A female subject, aged around 40 · dermoscopy of a skin lesion: 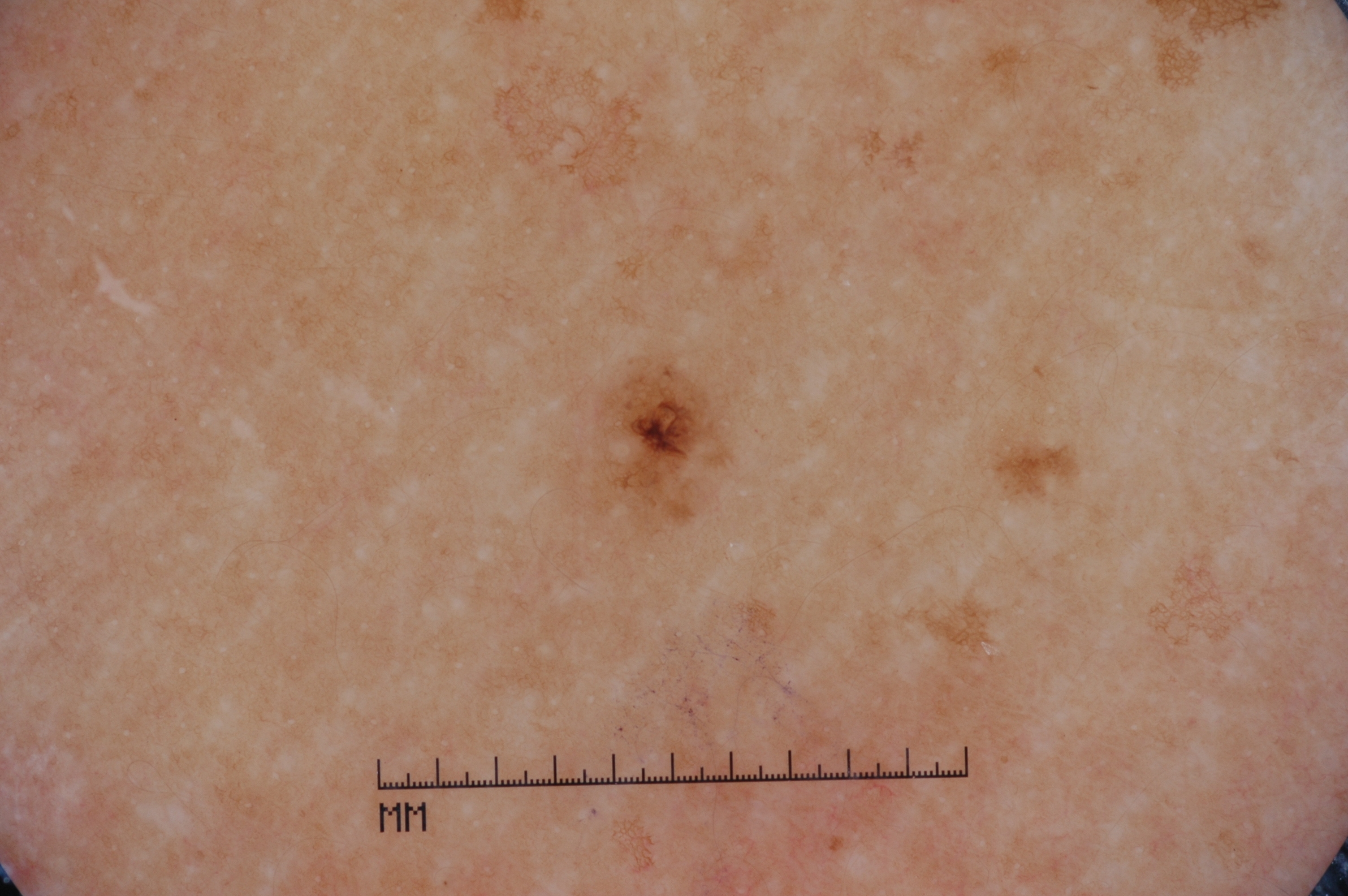As (left, top, right, bottom), the lesion is bounded by <bbox>590, 371, 716, 518</bbox>. Dermoscopy demonstrates pigment network. The diagnostic assessment was a melanocytic nevus.